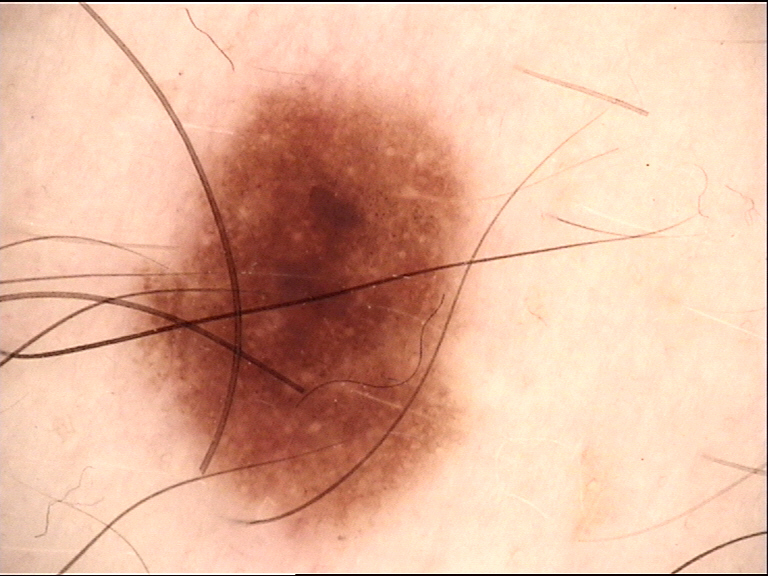Classified as a junctional nevus.